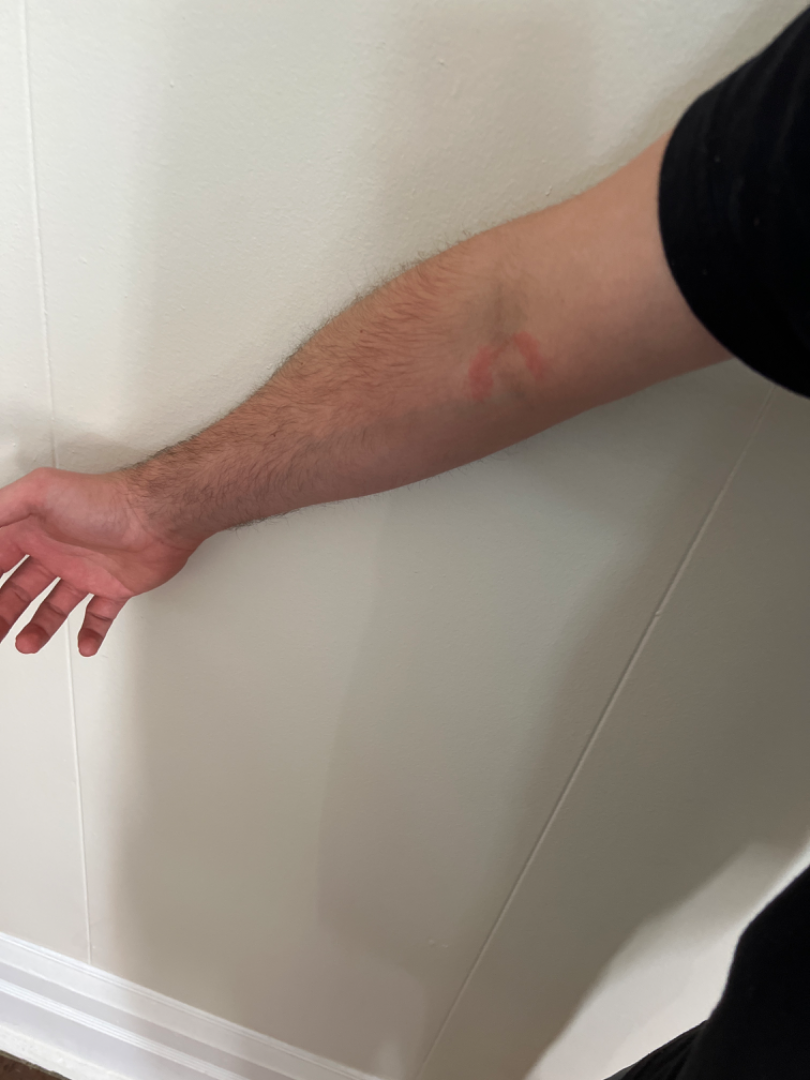The case was difficult to assess from the available photograph.